A close-up photograph:
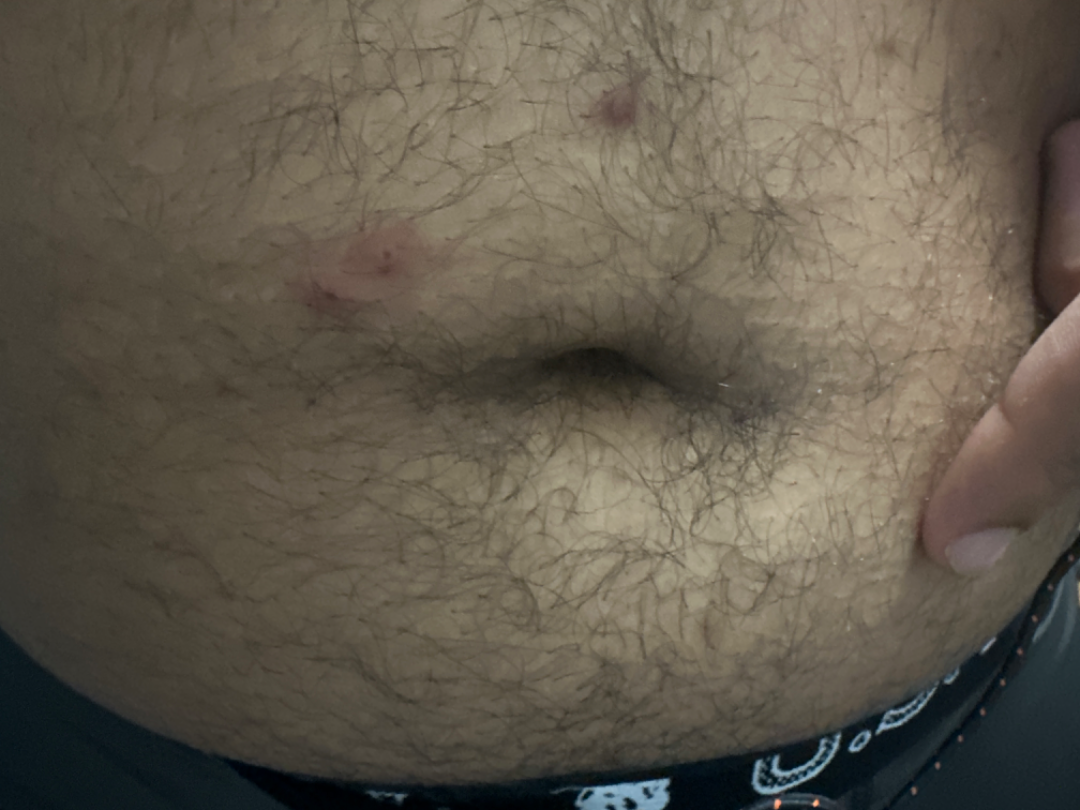assessment — ungradable on photographic review